The photograph is a close-up of the affected area. Fitzpatrick skin type I; lay reviewers estimated a Monk Skin Tone of 1. Female subject, age 18–29: 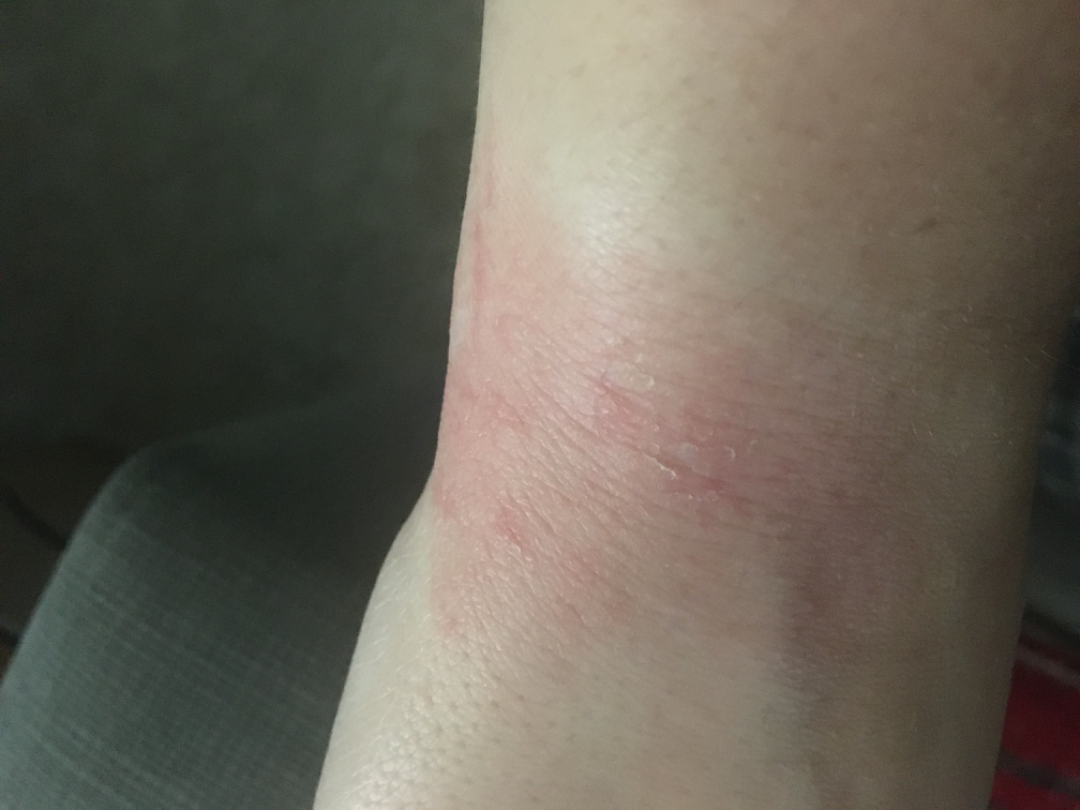diagnostic considerations: favoring Eczema; also raised was Irritant Contact Dermatitis.